Fitzpatrick phototype II. A male patient in their 60s. History notes alcohol use, prior malignancy (patient or family), and prior skin cancer (patient or family).
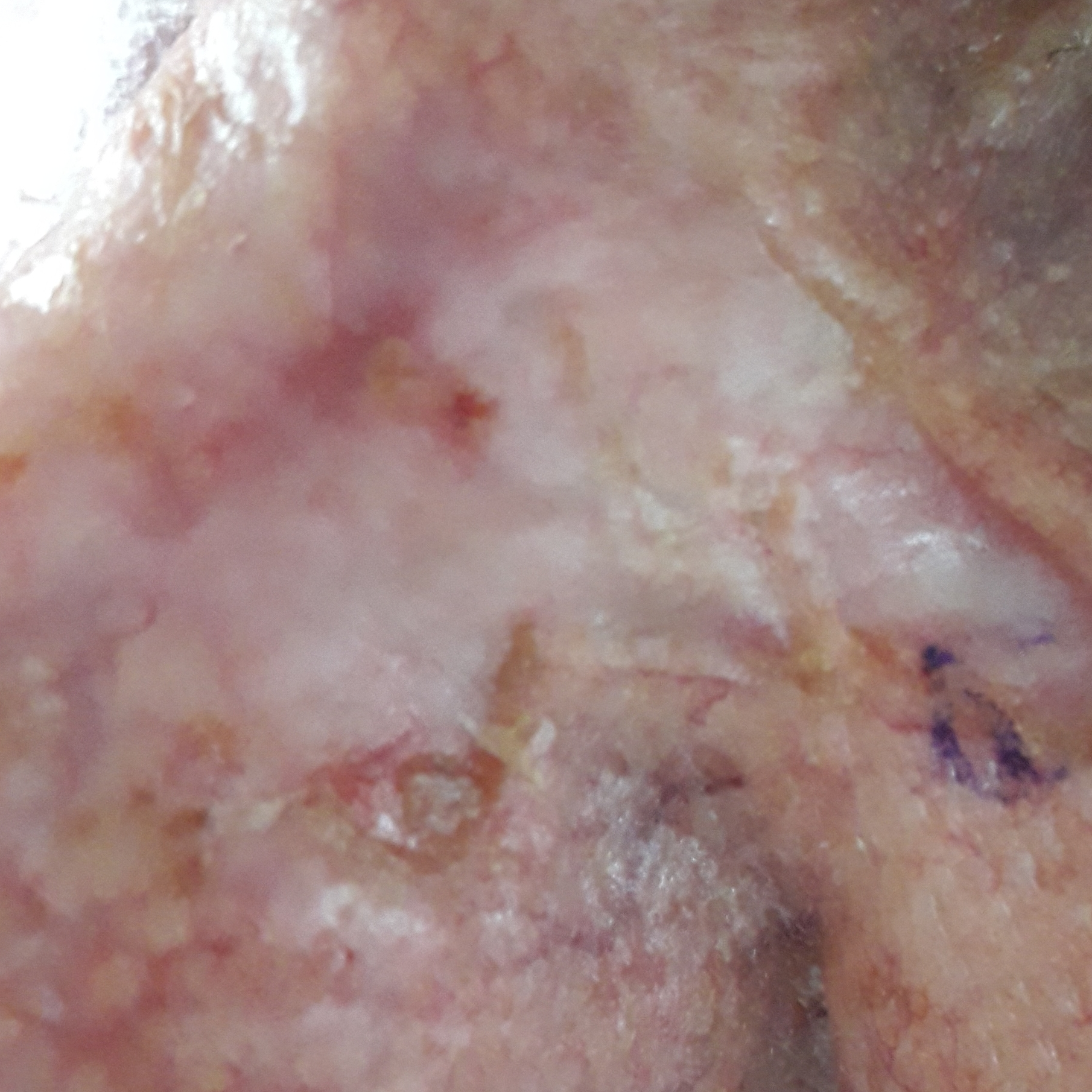Q: Where on the body is the lesion?
A: the face
Q: What does the patient describe?
A: bleeding, elevation, pain, growth, itching / no change in appearance
Q: What did the workup show?
A: basal cell carcinoma (biopsy-proven)